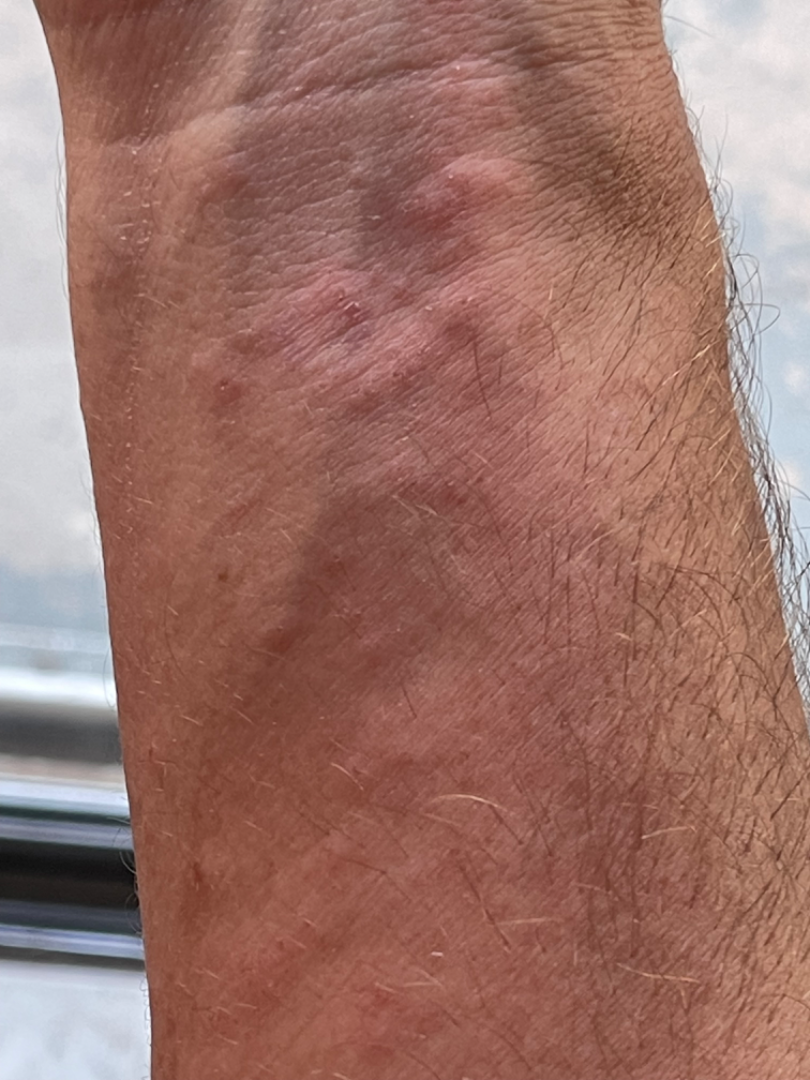| field | value |
|---|---|
| systemic symptoms | none reported |
| framing | close-up |
| body site | arm |
| self-categorized as | a rash |
| patient | male |
| dermatologist impression | three dermatologists each reviewed the case: the differential is split between Acute dermatitis, NOS; Eczema; and Contact dermatitis; a remote consideration is Allergic Contact Dermatitis |